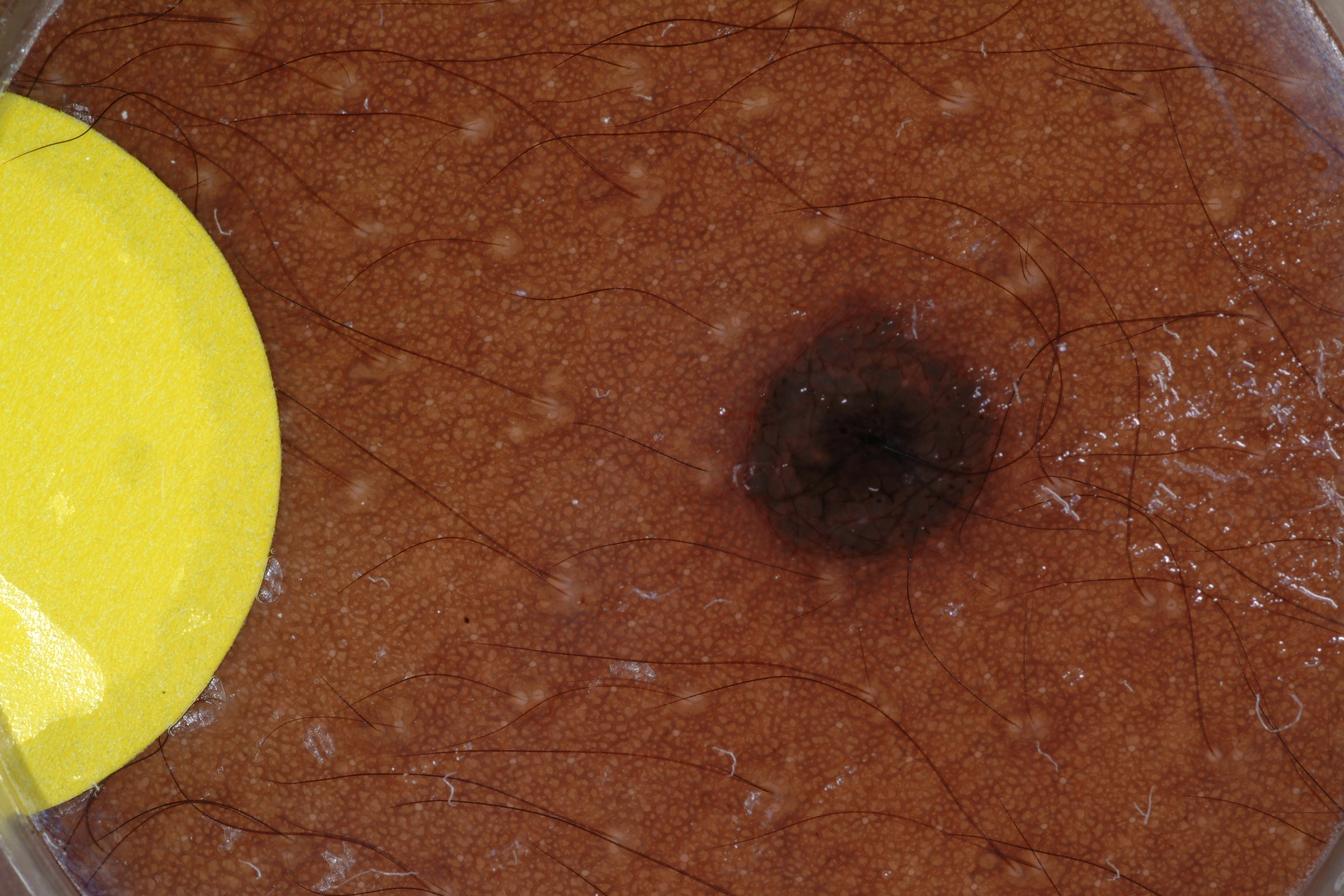A male subject, aged around 15.
A dermoscopic view of a skin lesion.
The lesion's extent is 710/294/1017/595.
Dermoscopic assessment notes no milia-like cysts, negative network, pigment network, streaks, or globules.
Clinically diagnosed as a melanocytic nevus, a benign lesion.